A patient 75 years of age. A smartphone photograph of a skin lesion — 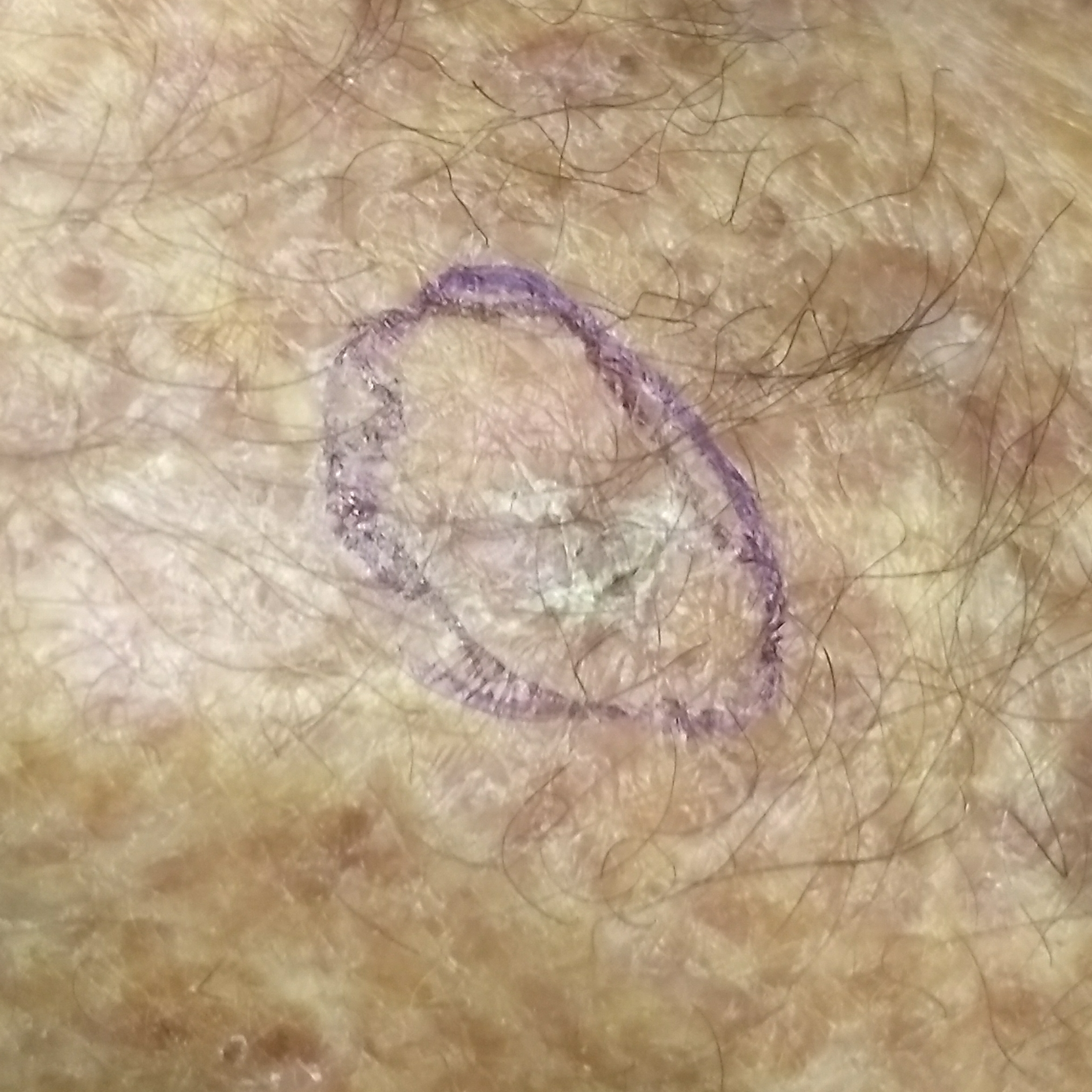Case summary: The lesion is located on a forearm. The patient reports that the lesion itches, but is not elevated and has not bled. Conclusion: The diagnostic impression was an actinic keratosis.